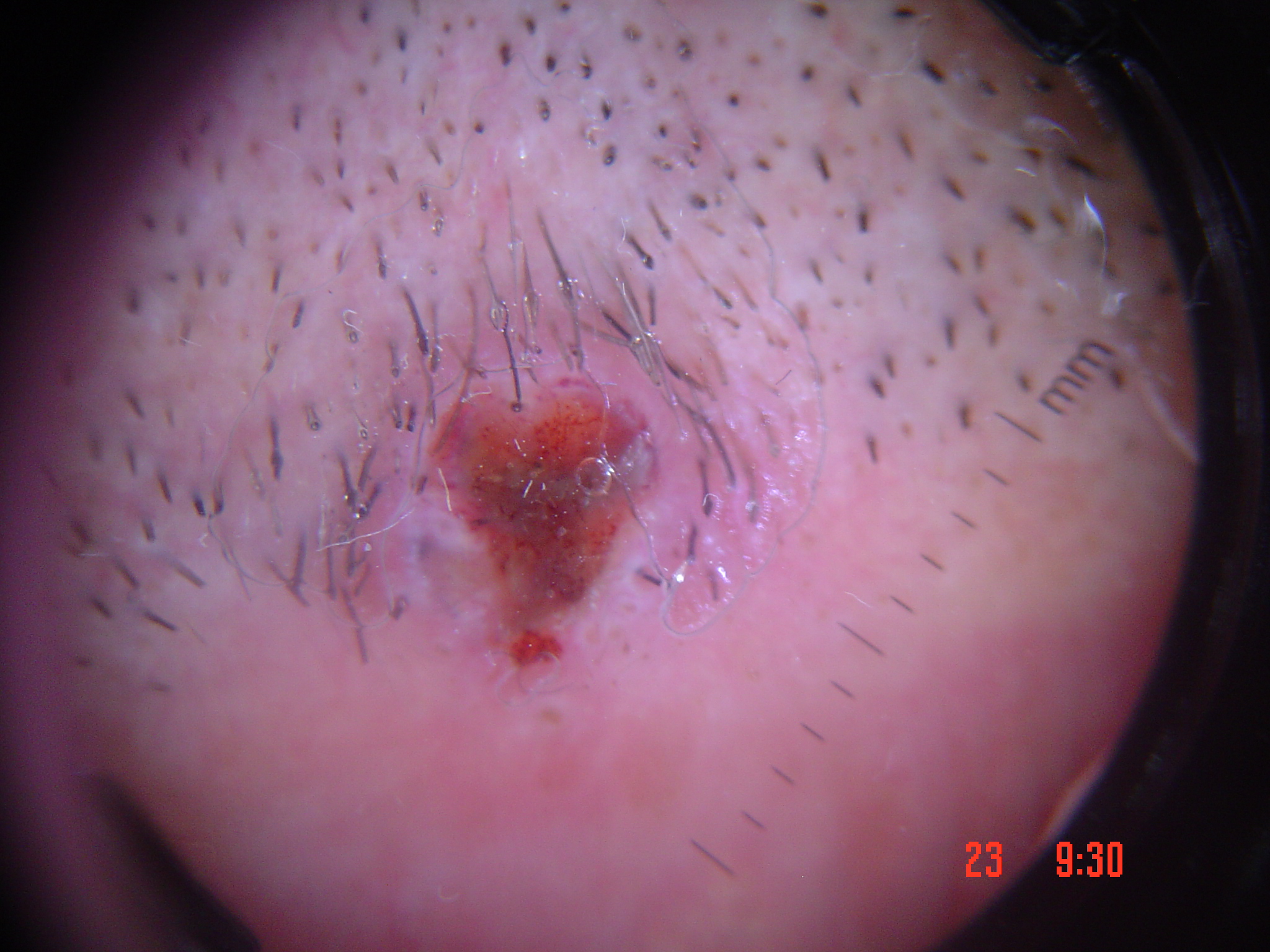Case:
- pathology: squamous cell carcinoma (biopsy-proven)